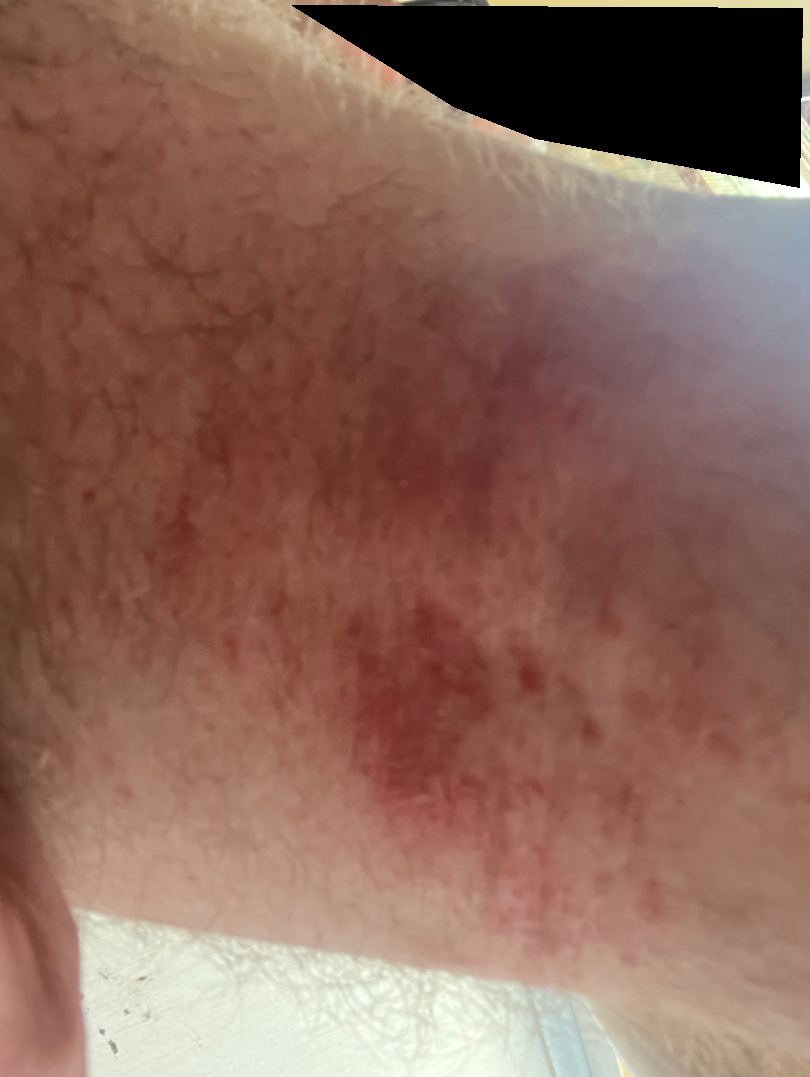{"shot_type": "at an angle", "body_site": "leg", "patient": "male, age 50–59", "differential": {"leading": ["Eczema"], "considered": ["Allergic Contact Dermatitis", "Irritant Contact Dermatitis"], "unlikely": ["Abrasion, scrape, or scab", "Acute dermatitis, NOS"]}}